A female subject approximately 85 years of age or older; a dermoscopy image of a single skin lesion — 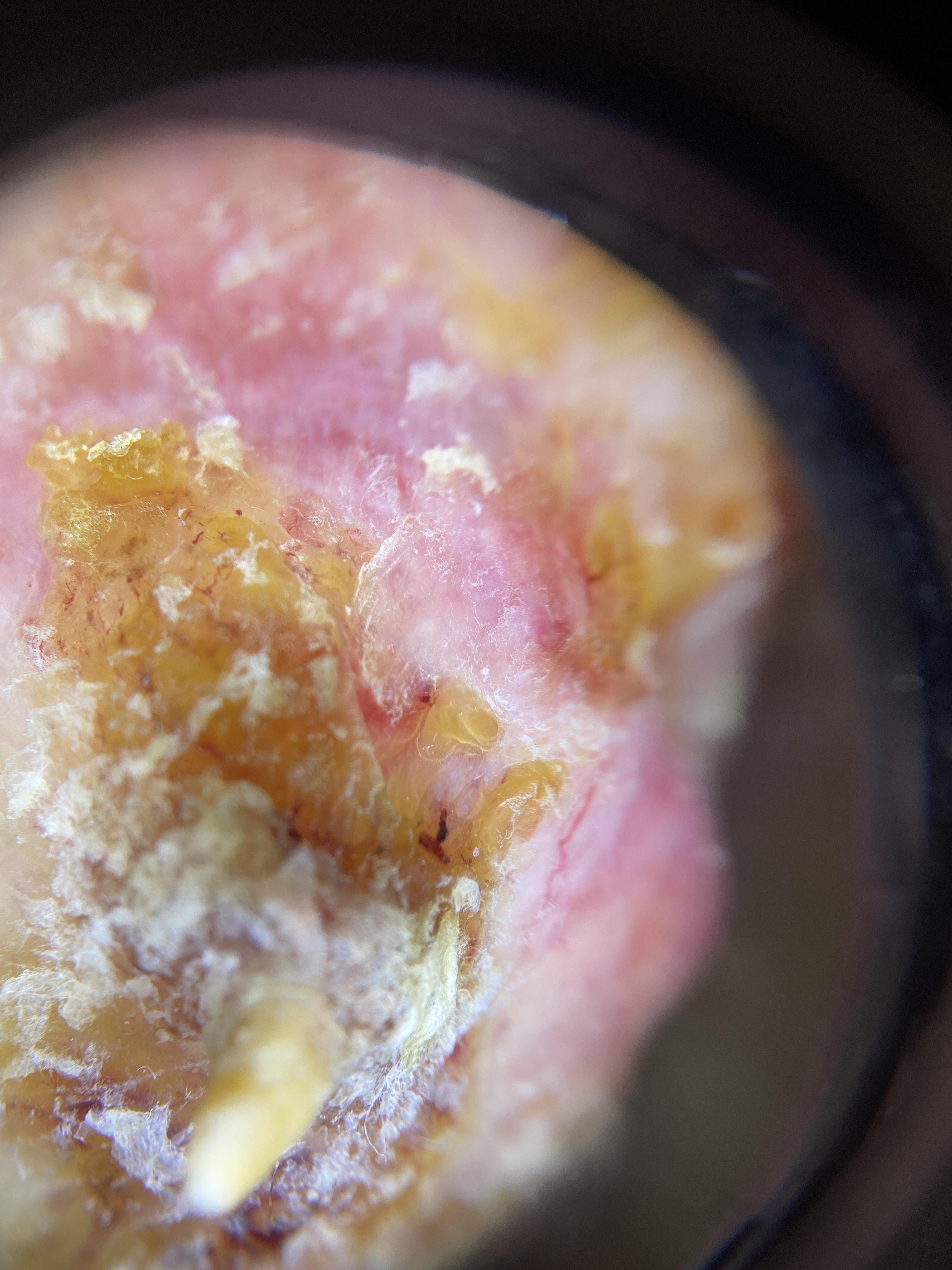Findings: The lesion is on the head or neck. Conclusion: Histopathologically confirmed as a squamous cell carcinoma.